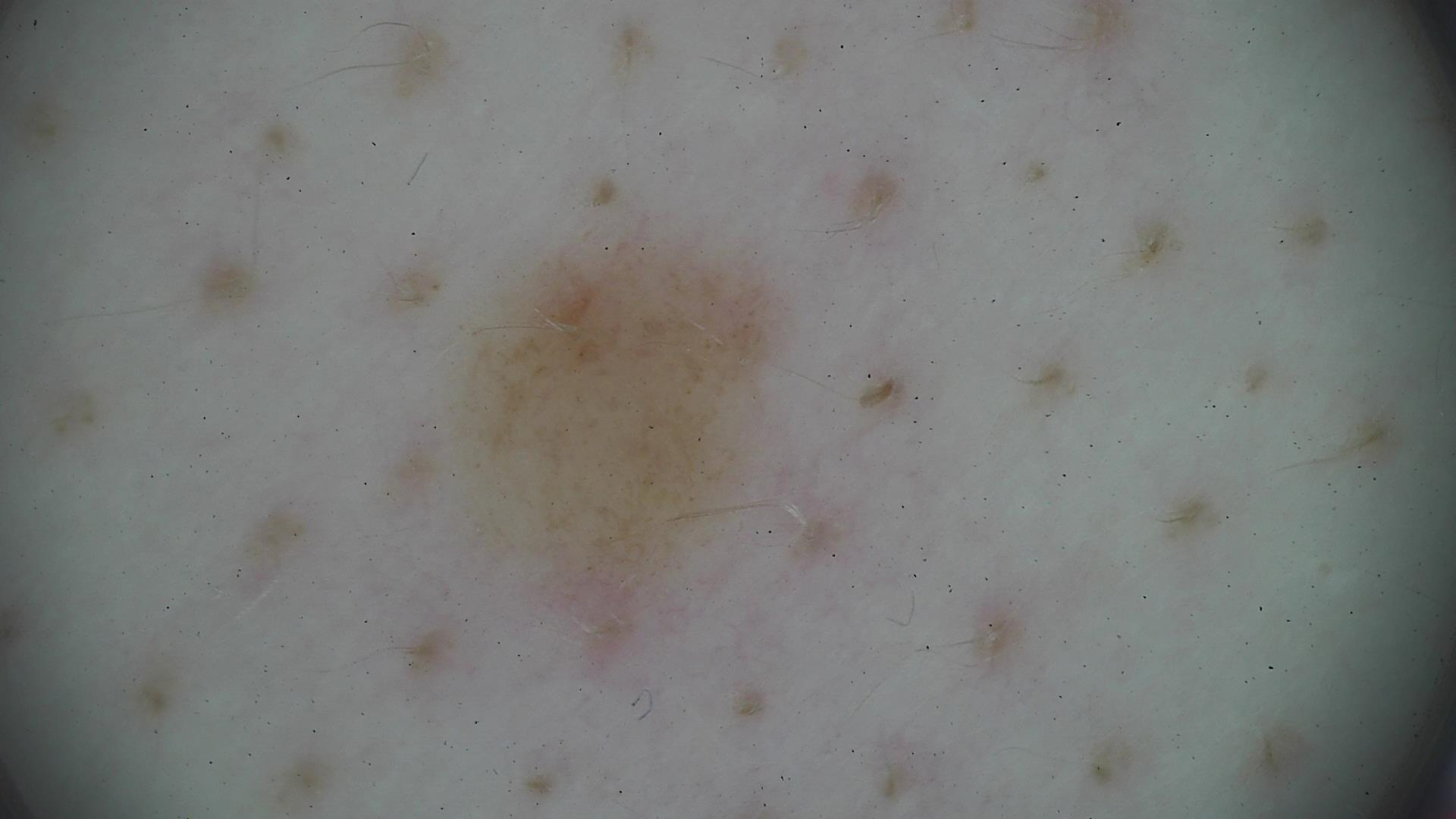- diagnosis · junctional nevus (expert consensus)